The subject is 40–49, male; a close-up photograph; texture is reported as flat; the patient indicates itching and darkening; the lesion involves the leg, arm, back of the torso and front of the torso; the patient indicates the condition has been present for one to four weeks; self-categorized by the patient as a rash:
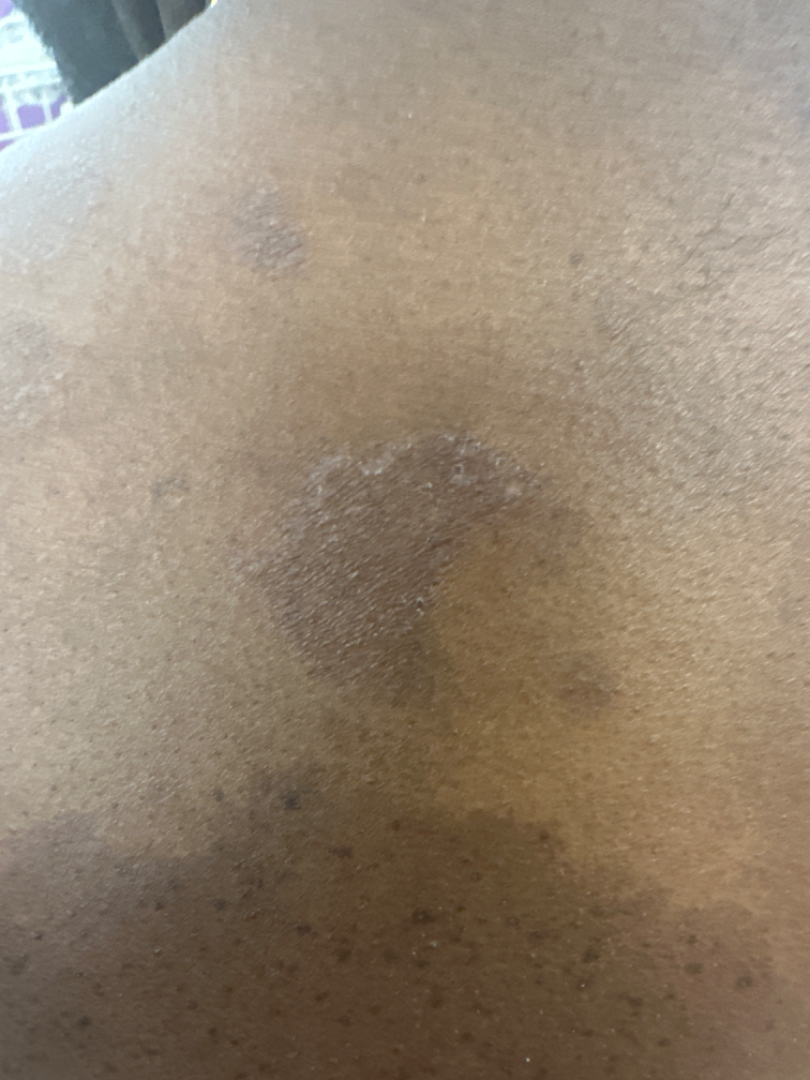Review:
On teledermatology review, the favored diagnosis is Eczema.